An image taken at an angle — 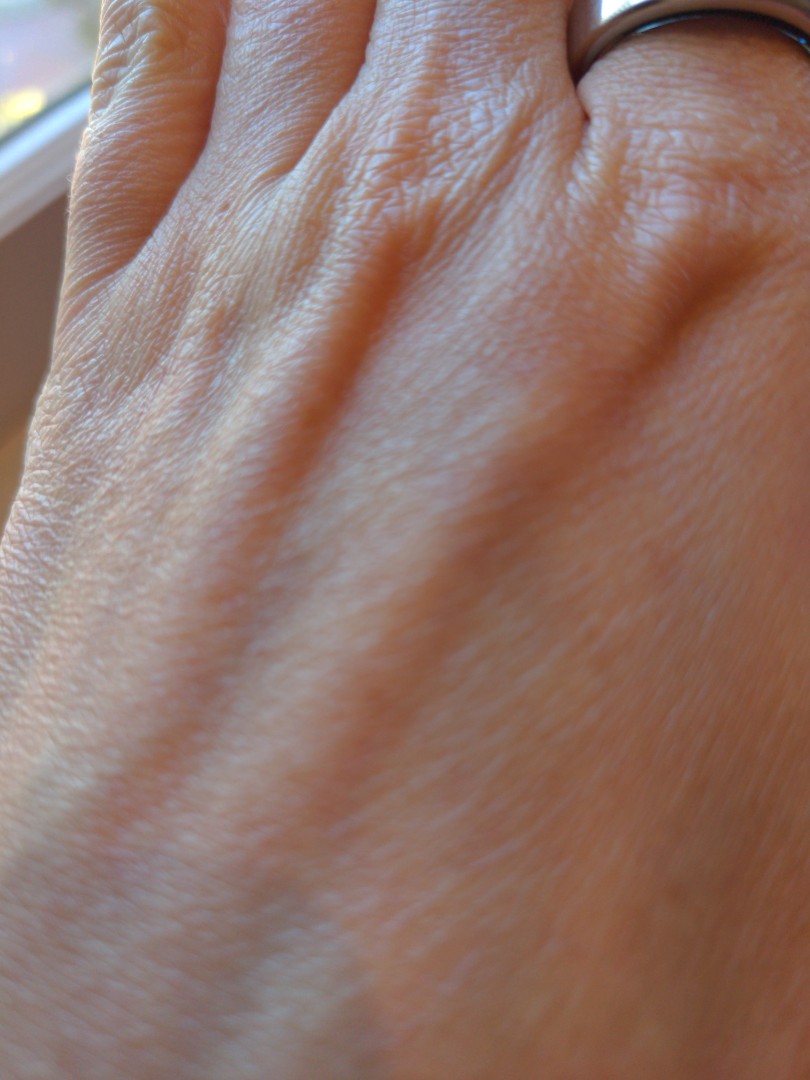Assessment: No discernible skin pathology was identified on dermatologist review.